A female subject aged 73-77, a dermoscopic close-up of a skin lesion.
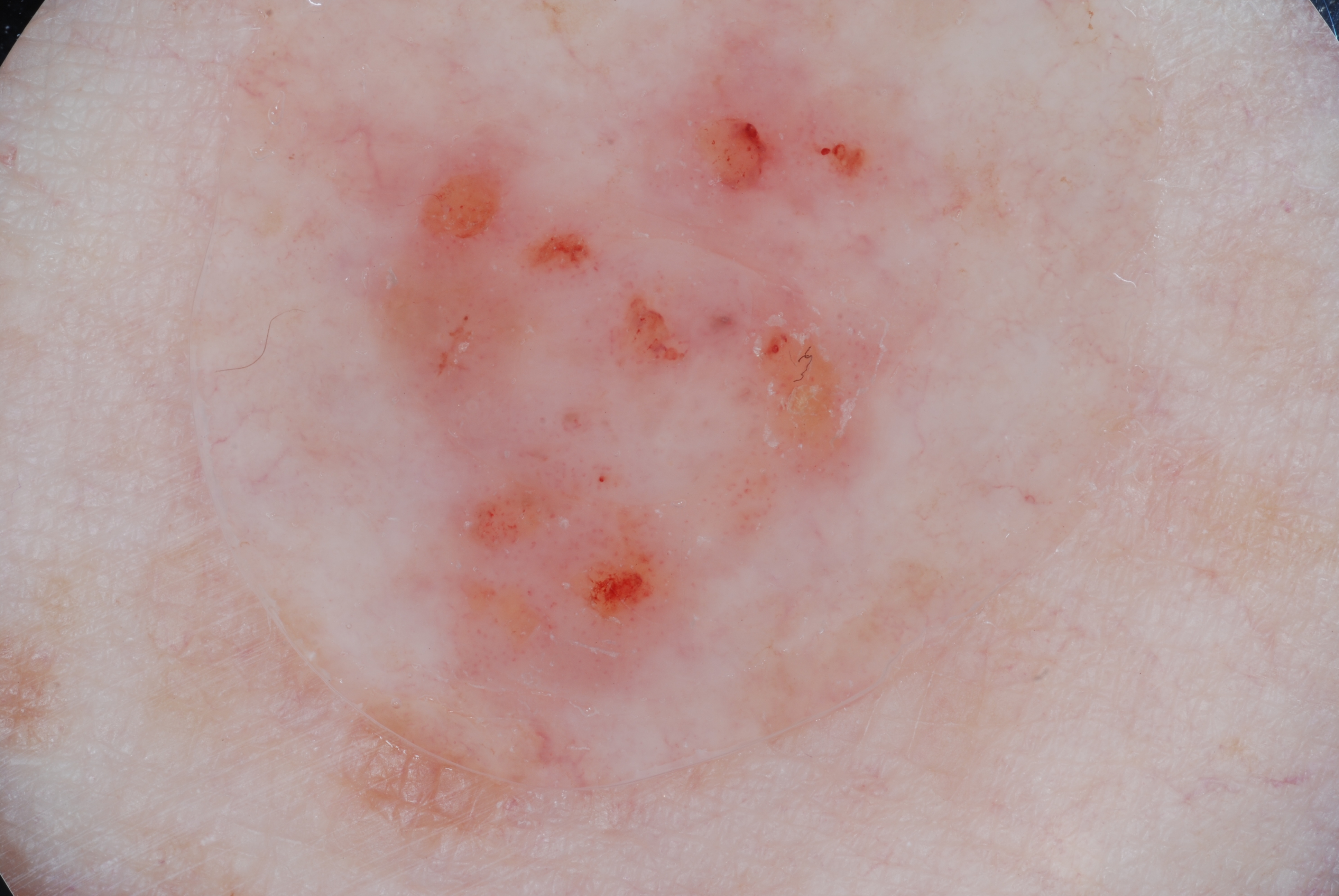Summary: Dermoscopic examination shows no milia-like cysts, streaks, pigment network, or negative network. With coordinates (x1, y1, x2, y2), the lesion is bounded by 286 0 976 851. Impression: The clinical diagnosis was a melanocytic nevus.